A dermoscopic close-up of a skin lesion.
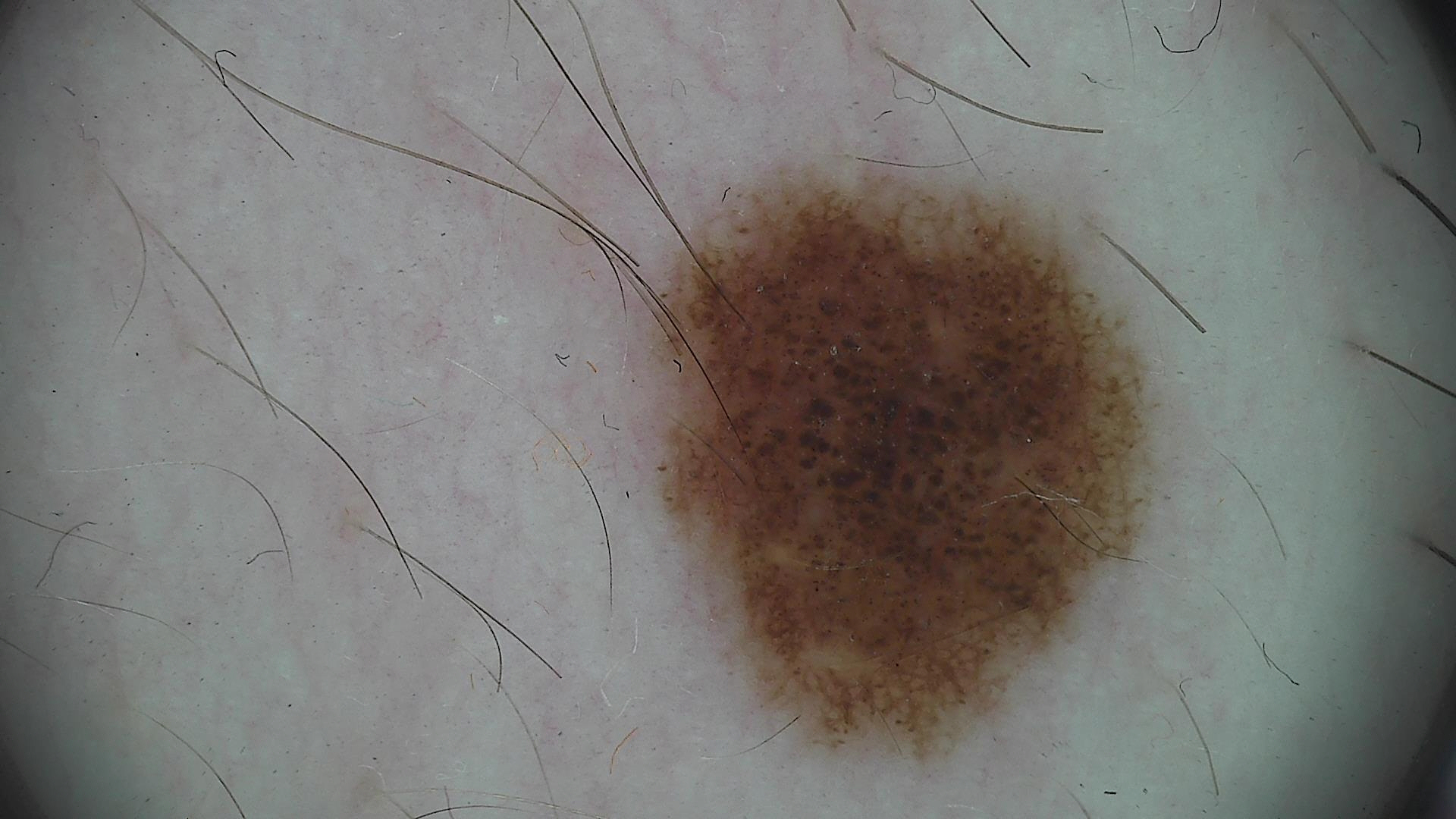Conclusion: The diagnosis was a dysplastic compound nevus.